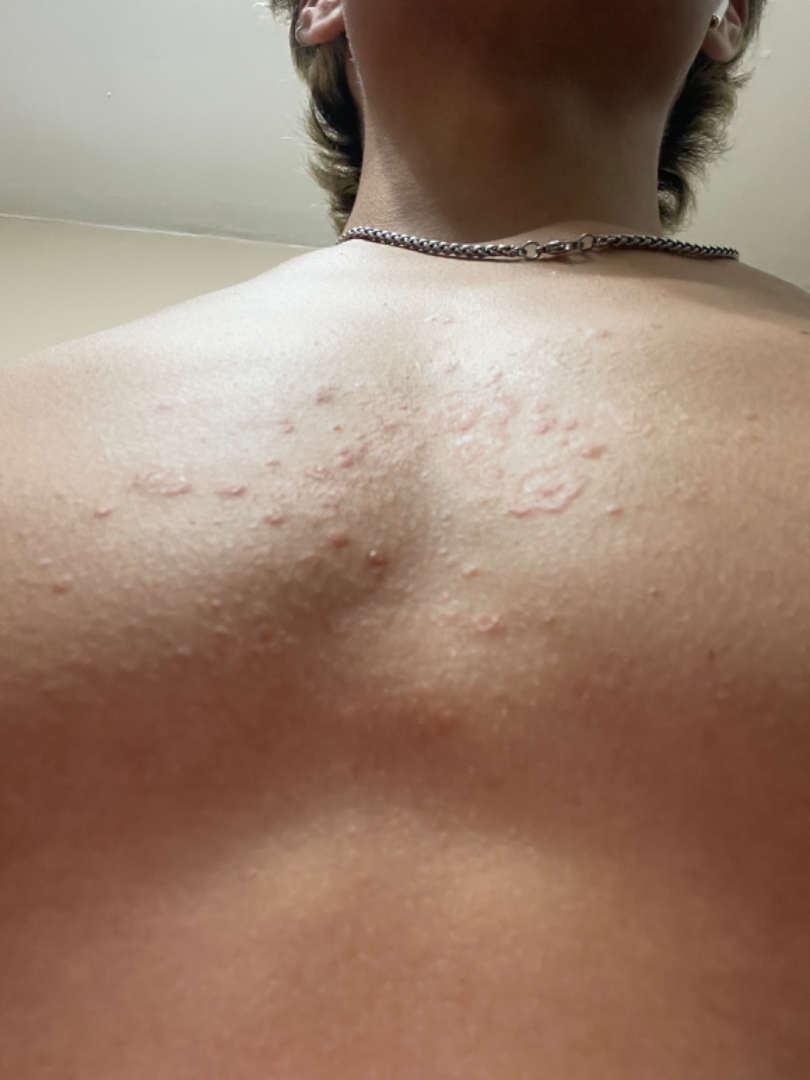{"systemic_symptoms": "none reported", "duration": "one to four weeks", "symptoms": ["enlargement", "bothersome appearance"], "shot_type": "at an angle", "differential": {"Erythema gyratum repens": 0.33, "Seborrheic Dermatitis": 0.33, "Erythema marginatum in acute rheumatic fever": 0.33}}